A dermoscopic photograph of a skin lesion:
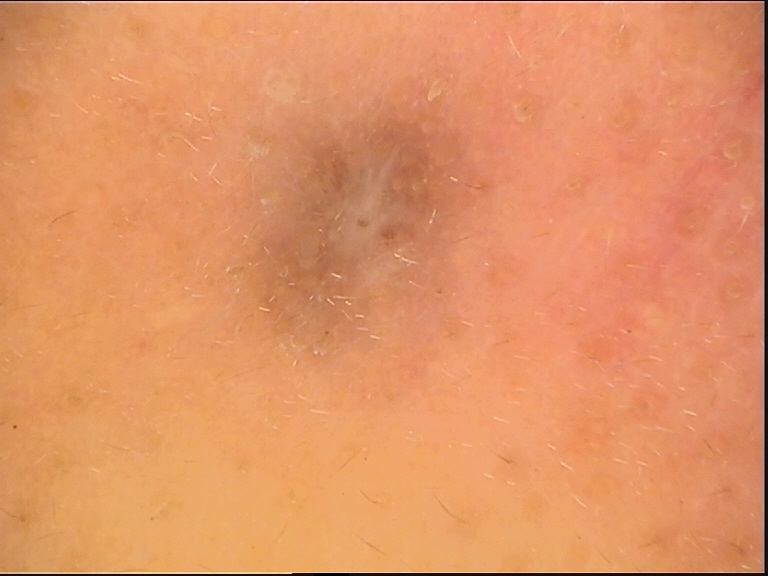Conclusion:
The diagnostic label was a dermatofibroma.